A dermatoscopic image of a skin lesion; skin type II; a female patient approximately 60 years of age — 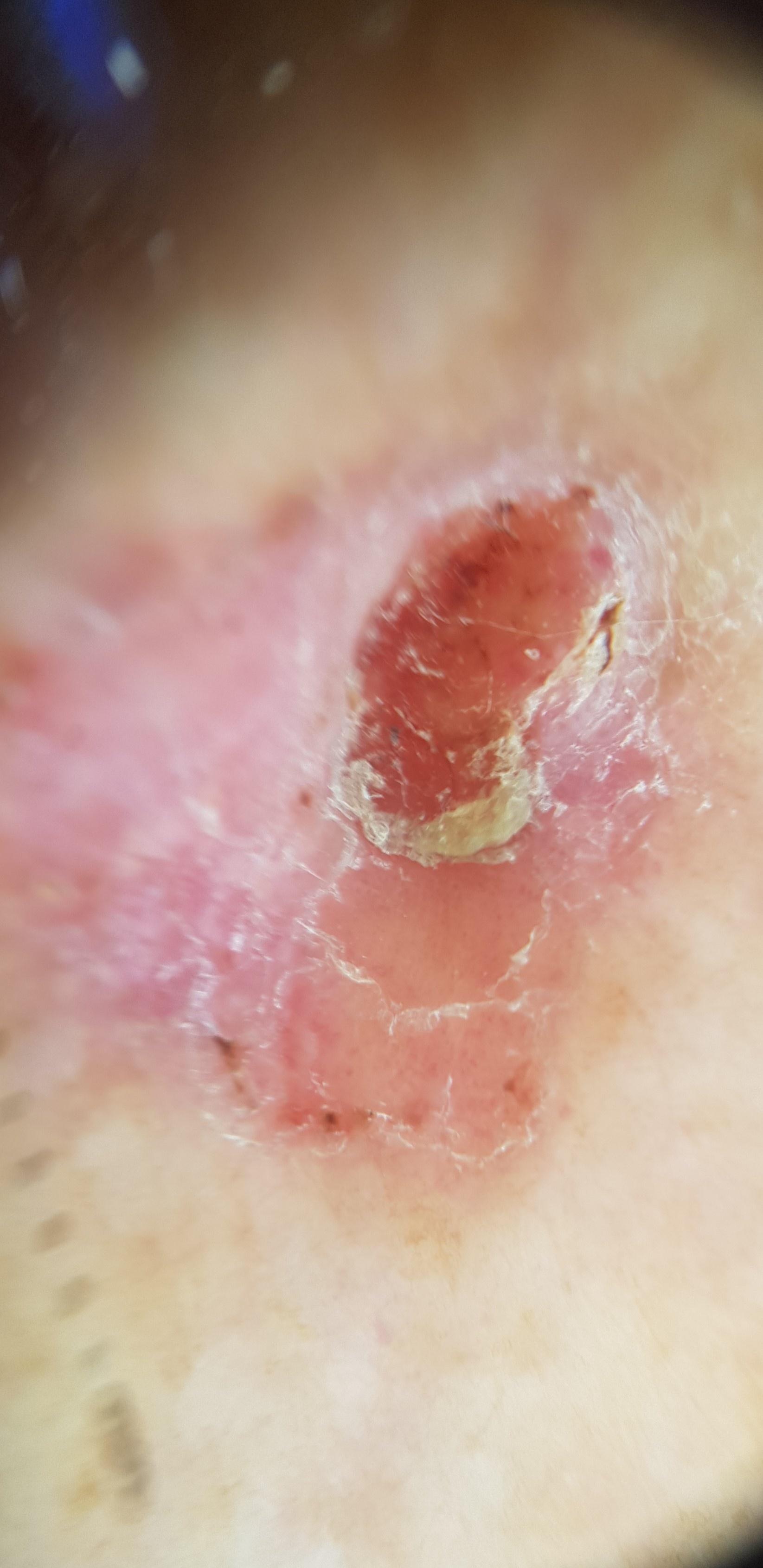lesion_location:
  region: a lower extremity
diagnosis:
  name: Basal cell carcinoma
  malignancy: malignant
  confirmation: histopathology
  lineage: adnexal